A dermoscopic photograph of a skin lesion.
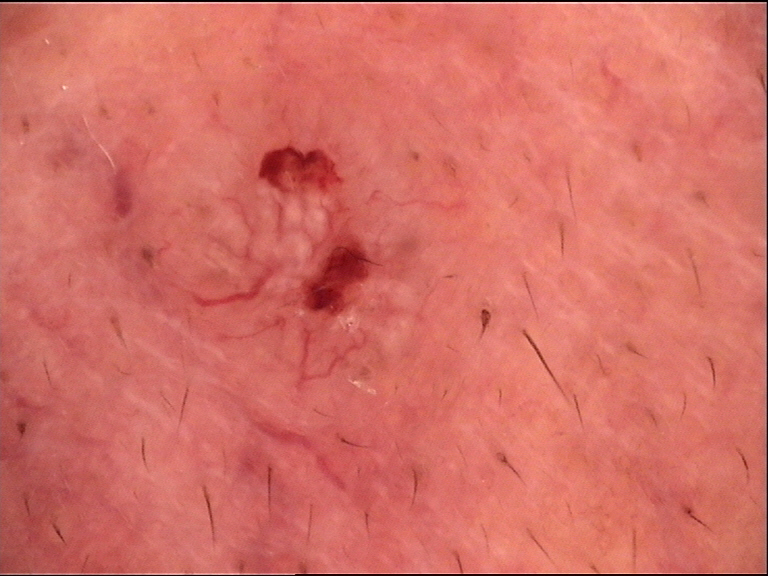diagnosis = basal cell carcinoma (biopsy-proven).